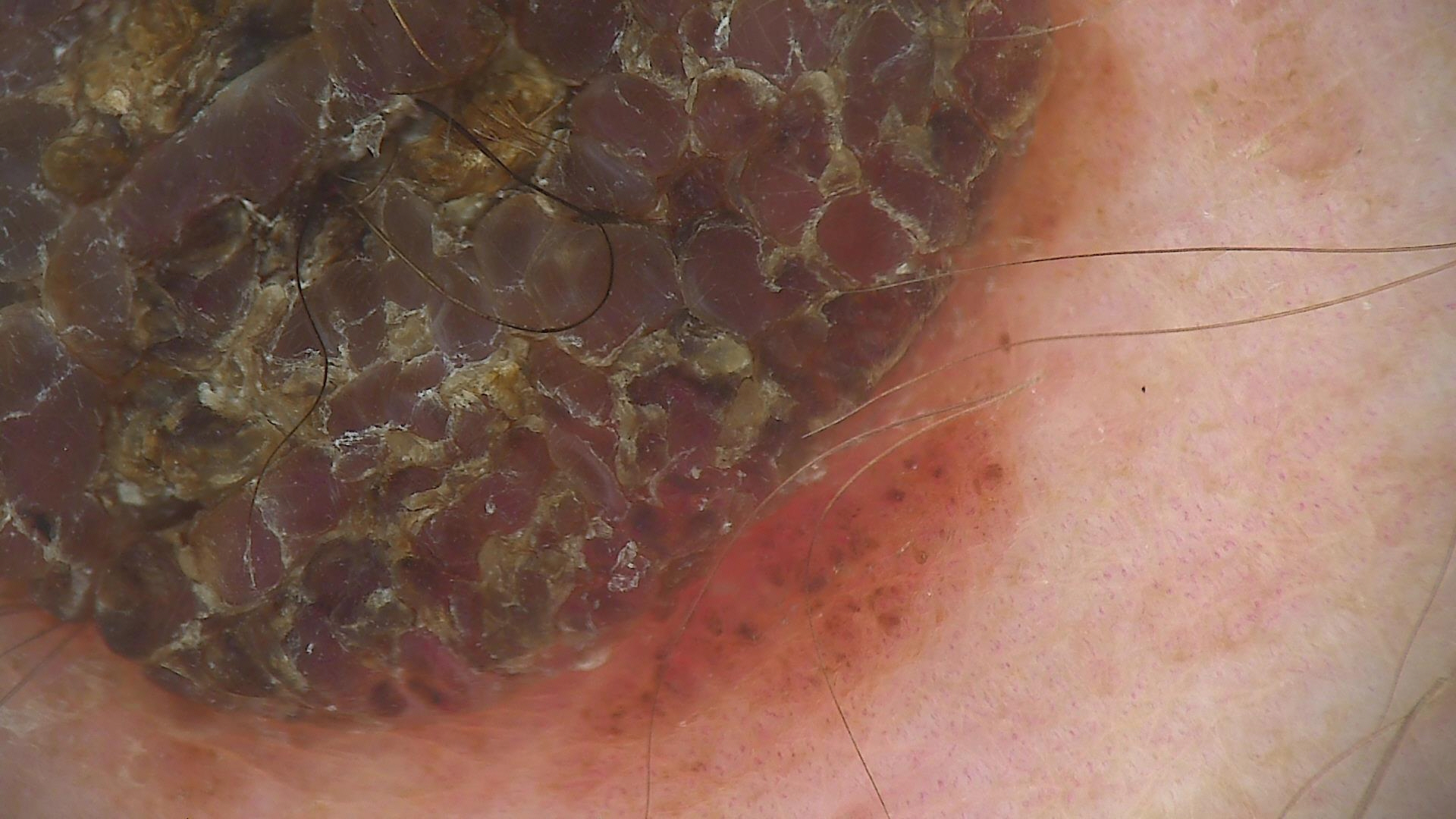Summary:
The architecture is that of a banal lesion.
Impression:
Classified as a congenital compound nevus.